The patient notes the lesion is raised or bumpy; male patient, age 30–39; the lesion involves the leg; the patient considered this a rash; an image taken at a distance; the condition has been present for more than one year; the lesion is associated with itching — 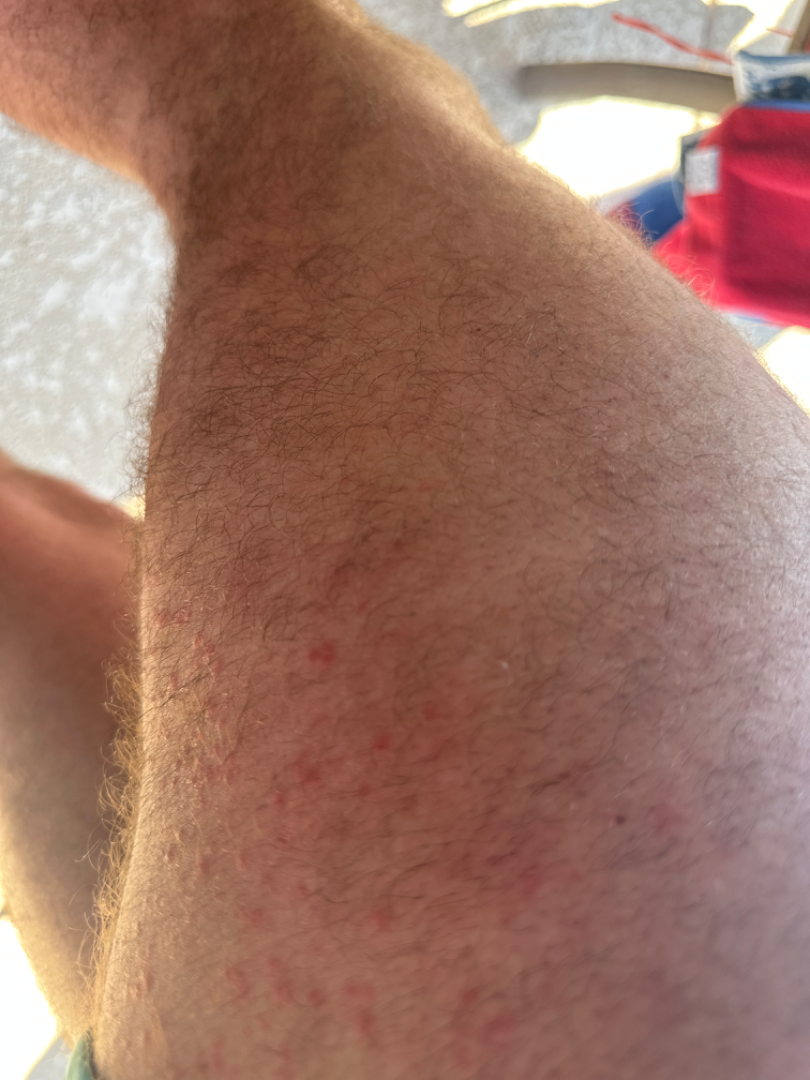Findings: The dermatologist could not determine a likely condition from the photograph alone.